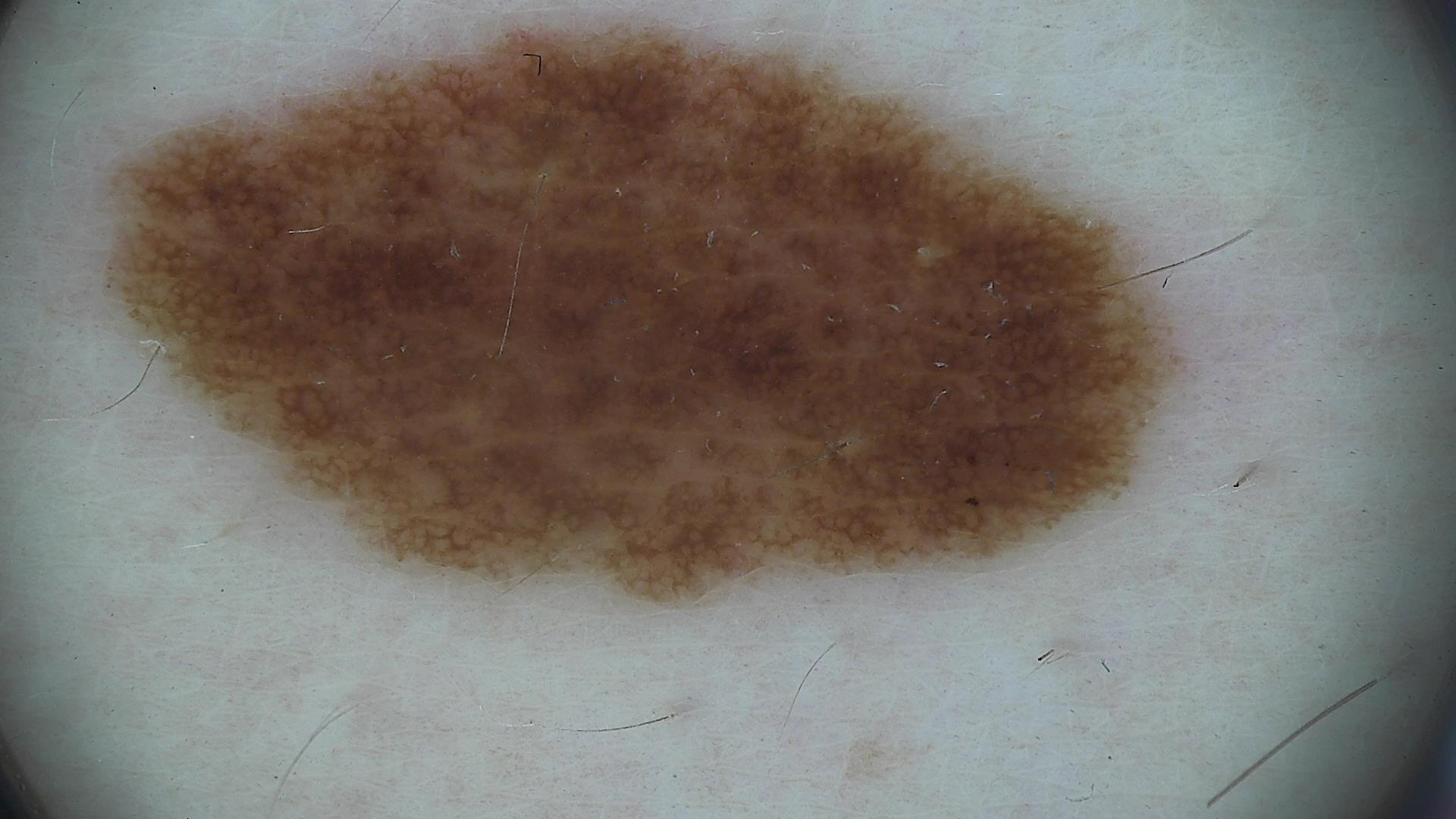A dermoscopy image of a single skin lesion.
The diagnostic label was a benign lesion — a dysplastic junctional nevus.